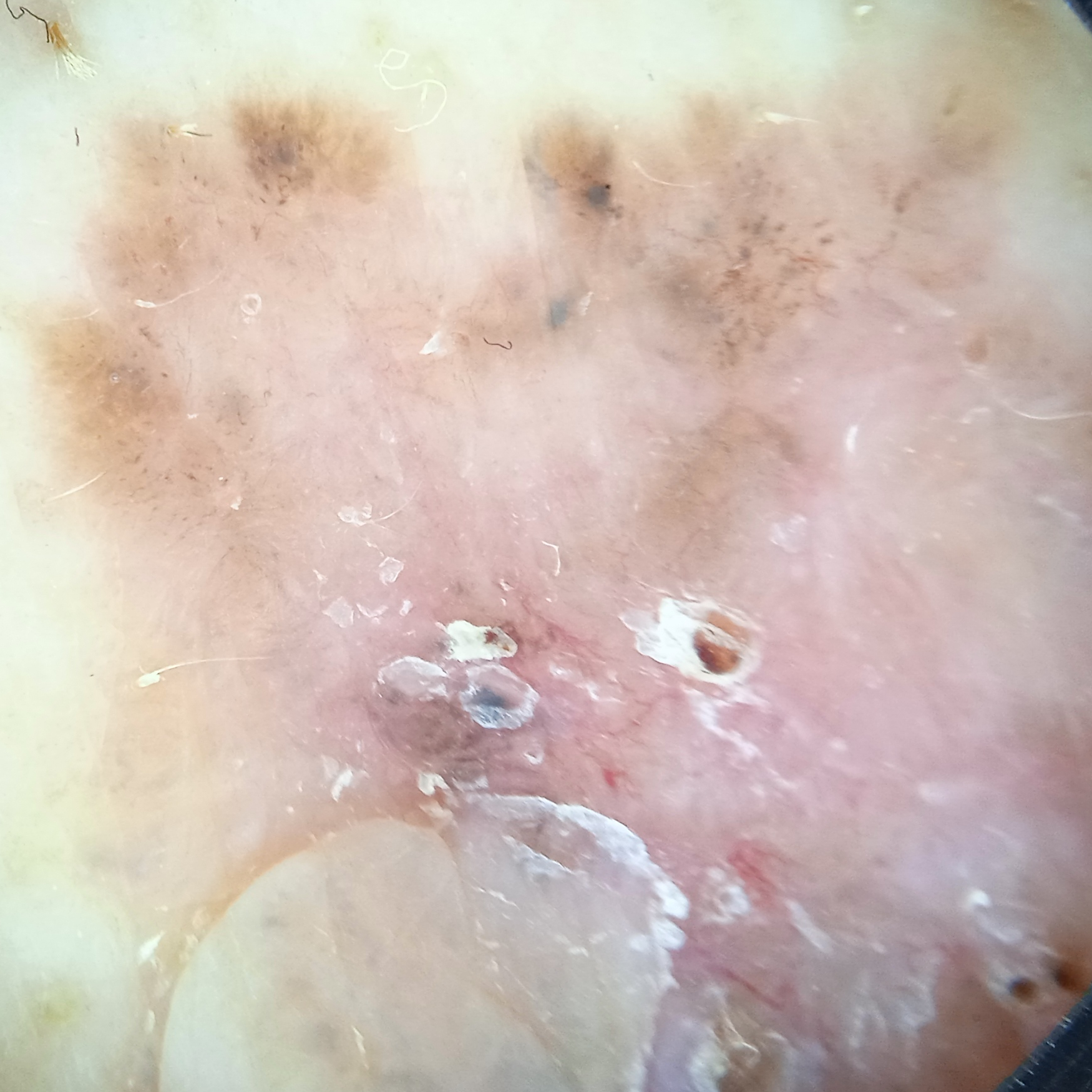{
  "sun_reaction": "skin tans without first burning",
  "mole_burden": "a moderate number of melanocytic nevi",
  "lesion_location": "the back",
  "lesion_size": {
    "diameter_mm": 22.1
  },
  "diagnosis": {
    "name": "basal cell carcinoma",
    "malignancy": "malignant",
    "unanimous": false,
    "certainty": "good"
  }
}